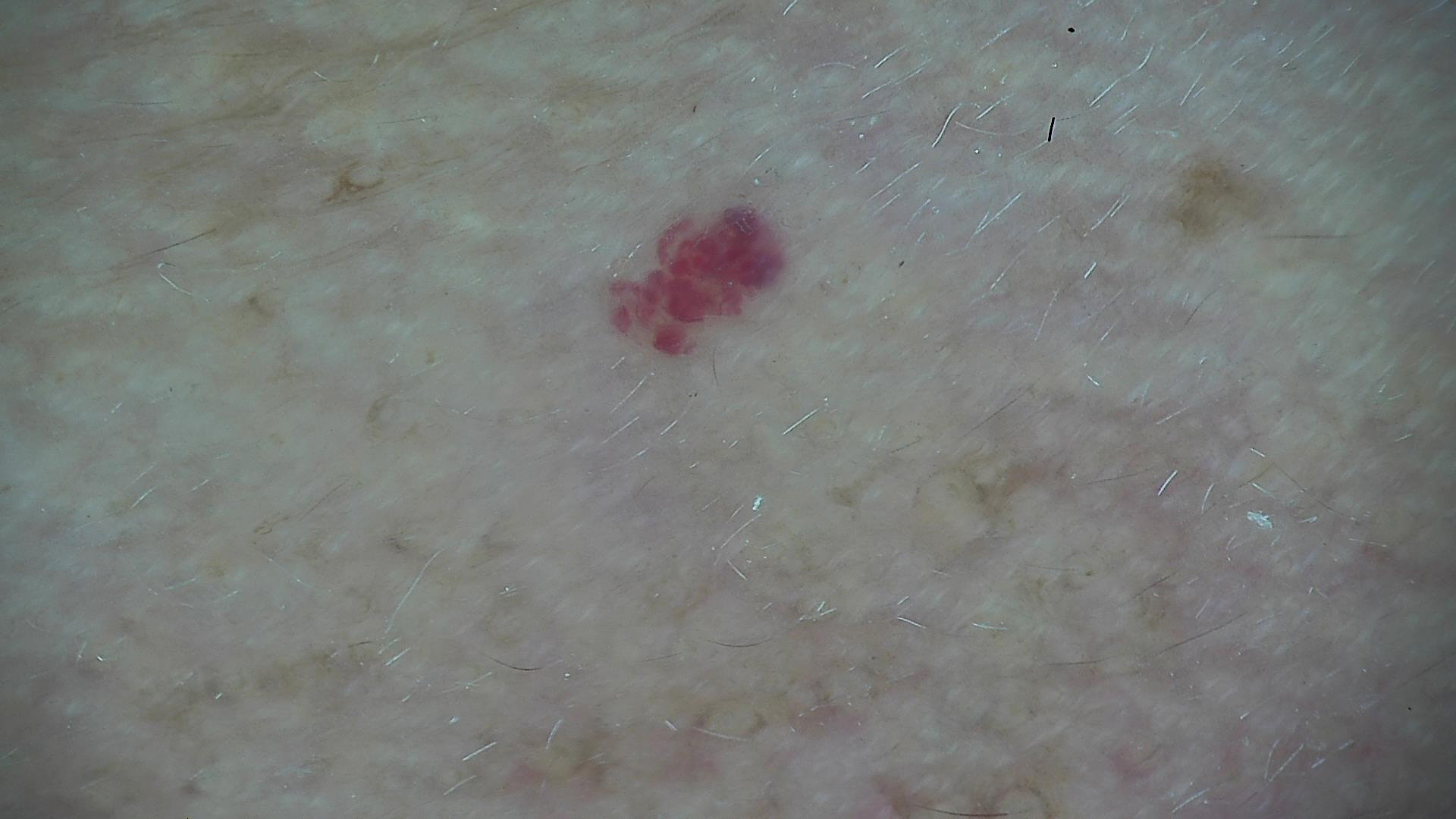label=hemangioma (expert consensus).